A male patient aged approximately 85 or older: 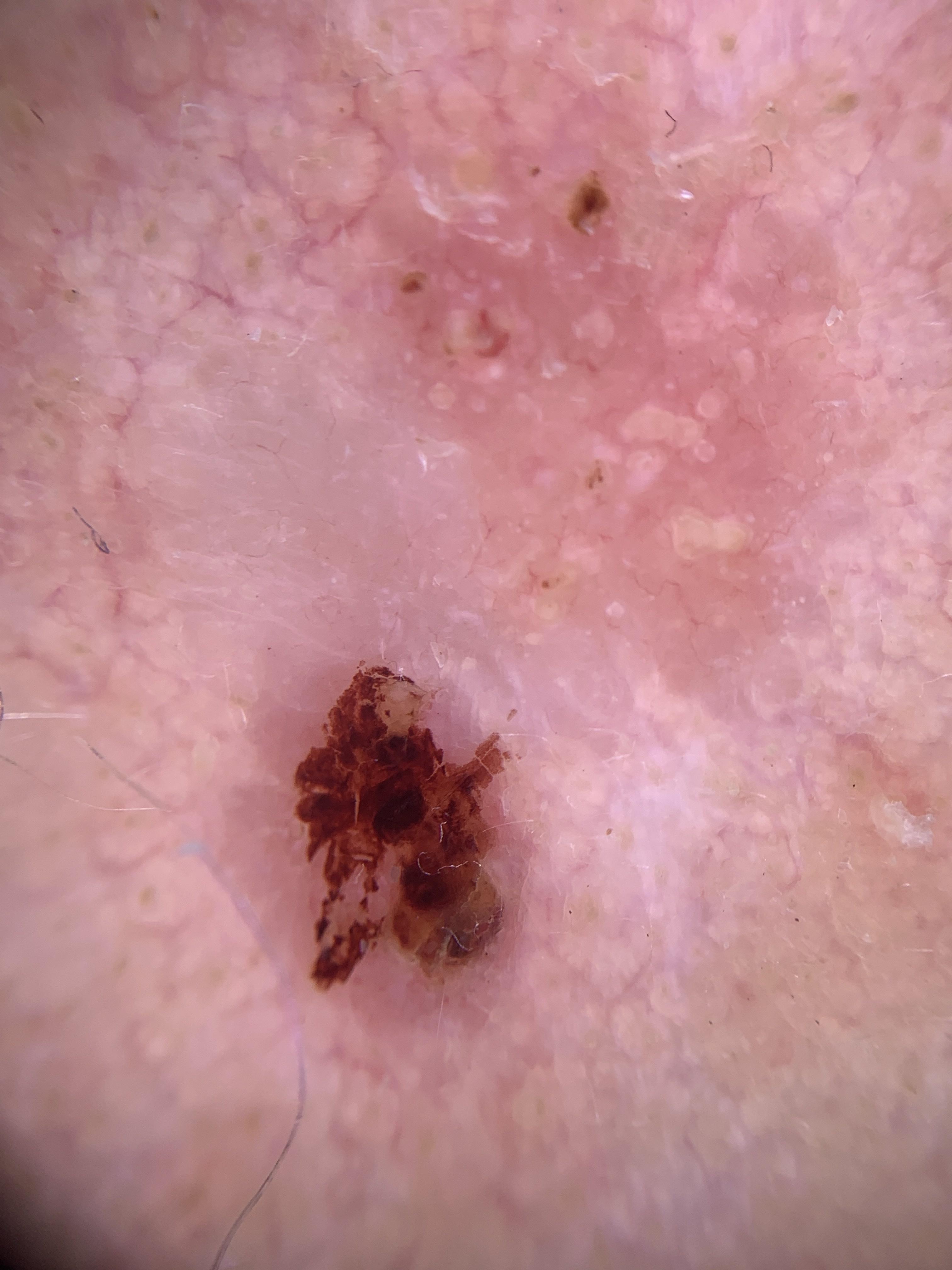| field | value |
|---|---|
| location | the head or neck |
| pathology | Basal cell carcinoma (biopsy-proven) |